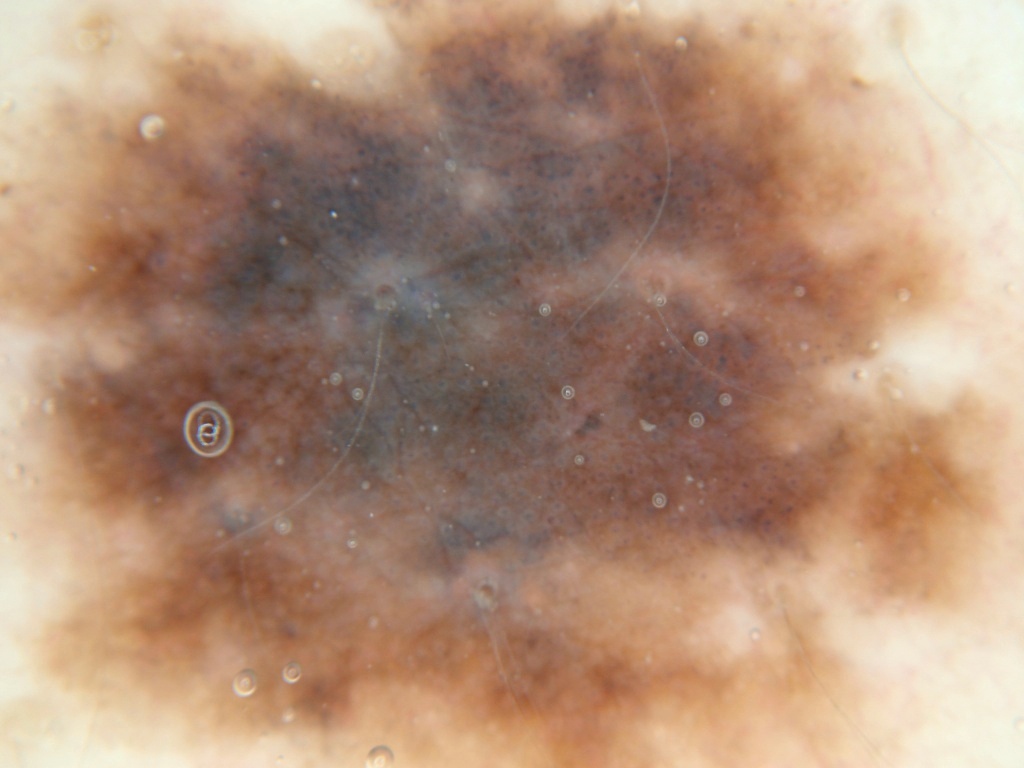Summary: A dermoscopic view of a skin lesion. The lesion extends across almost the whole field of view. Impression: The diagnostic assessment was a benign lesion.